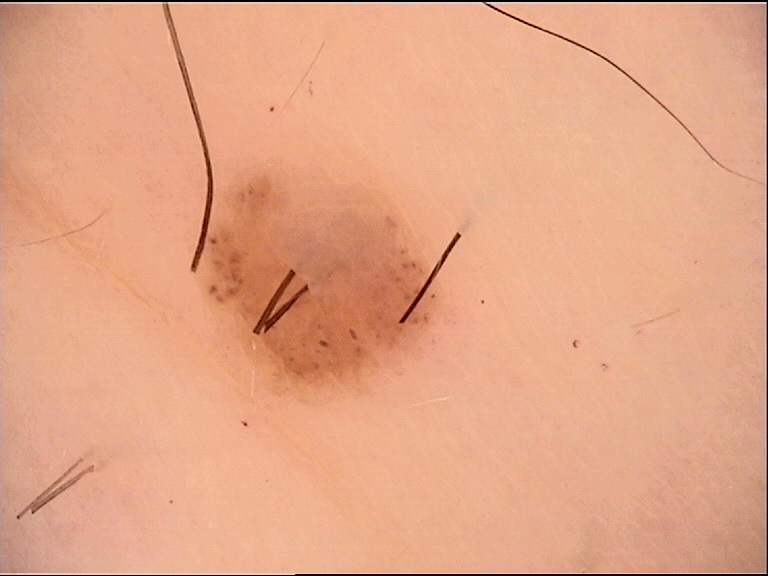A dermoscopic image of a skin lesion.
The morphology is that of a banal lesion.
Classified as a compound nevus.